The subject is a female aged around 65, a dermoscopy image of a single skin lesion — 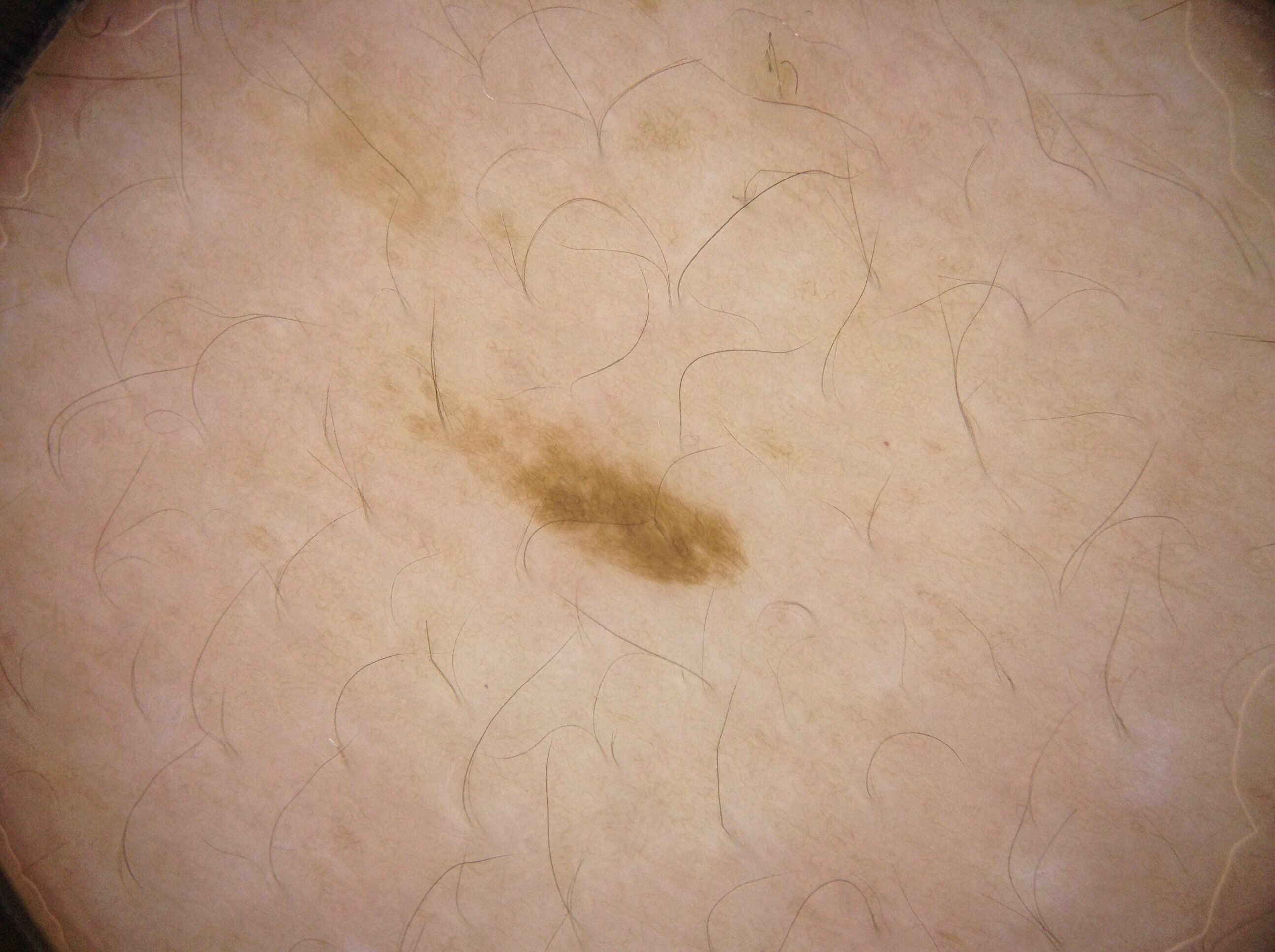Findings:
* bounding box · [371,339,757,598]
* features · pigment network
* diagnosis · a seborrheic keratosis, a benign lesion